Collected as part of a research study, without a referral diagnosis; few moles overall by the patient's own estimate; the patient reports a personal history of cancer, no immunosuppression, and no personal history of skin cancer; a male subject 78 years old; a dermatoscopic image of a skin lesion.
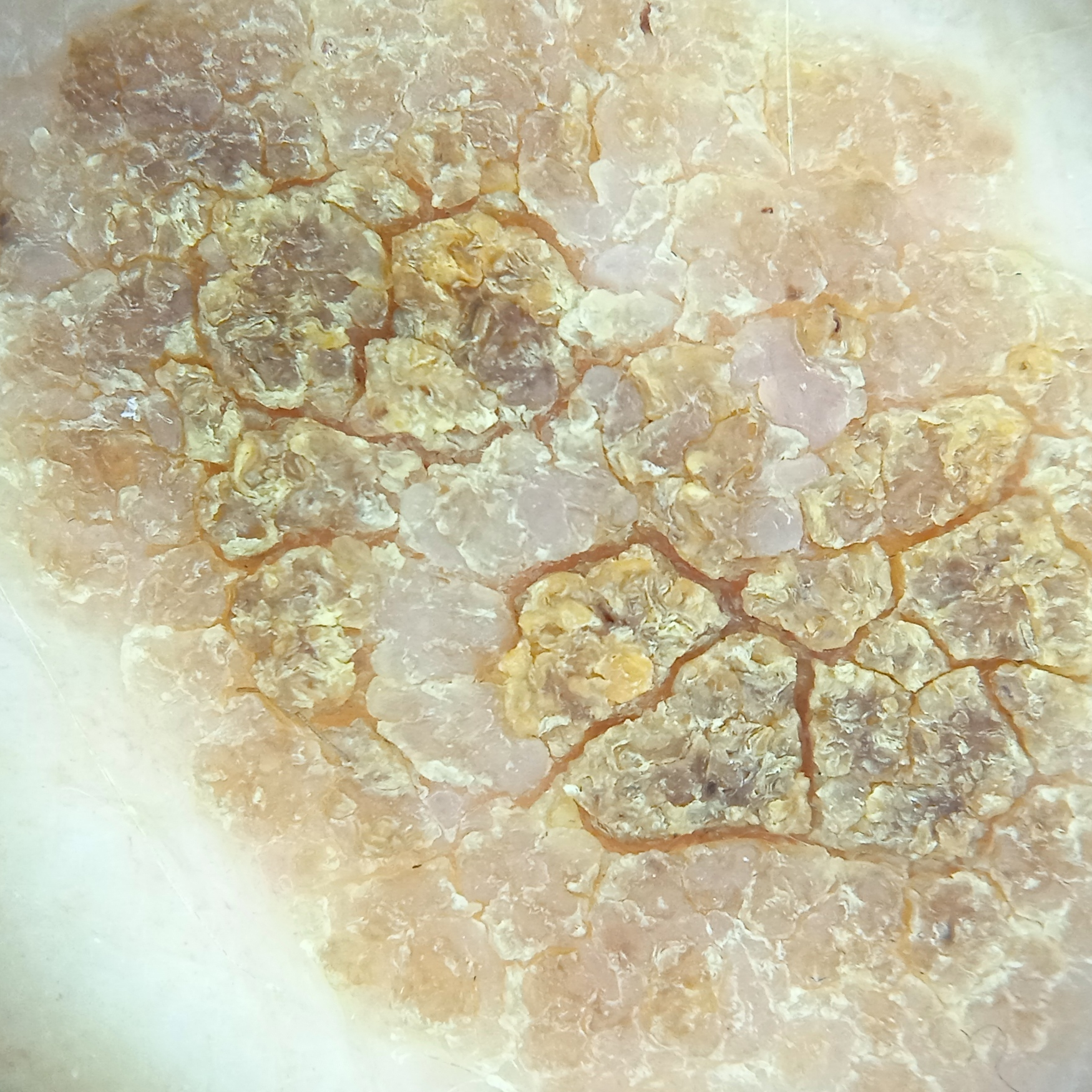Findings:
Located on the back.
Conclusion:
The dermatologists' assessment was a seborrheic keratosis.